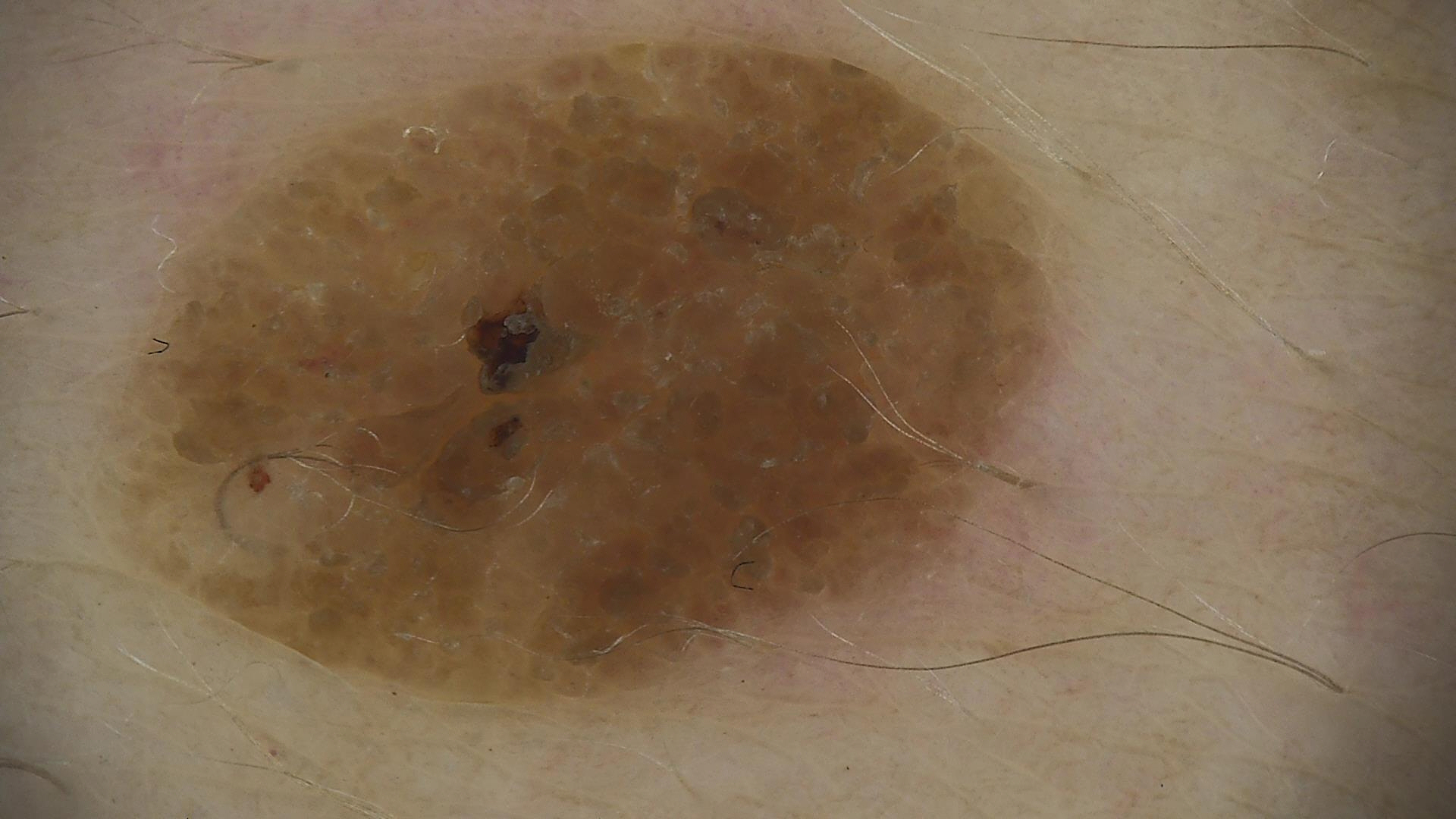image type=dermoscopy | classification=keratinocytic | class=seborrheic keratosis (expert consensus).